The photograph is a close-up of the affected area, the condition has been present for one to four weeks, symptoms reported: itching, the contributor notes the lesion is raised or bumpy, the patient described the issue as a rash, the front of the torso and leg are involved, the patient is a female aged 18–29, no associated systemic symptoms reported — 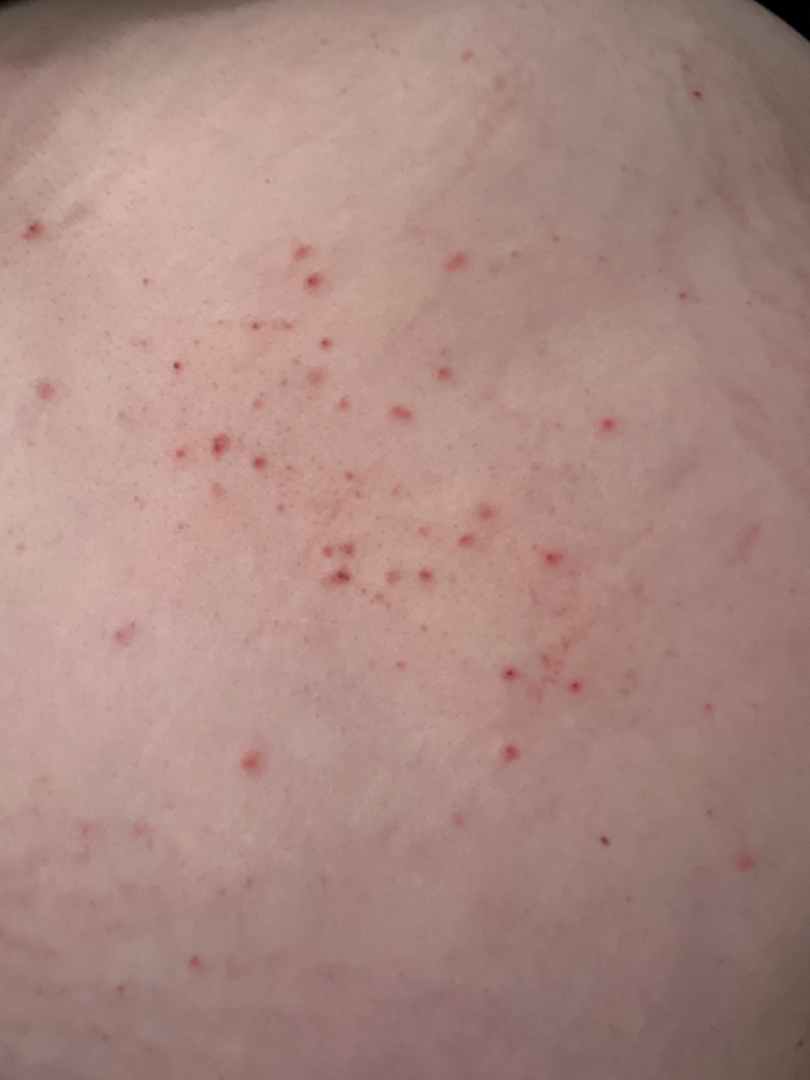<dermatology_case>
<differential>
  <tied_lead>Scabies, Folliculitis, Eczema</tied_lead>
</differential>
</dermatology_case>